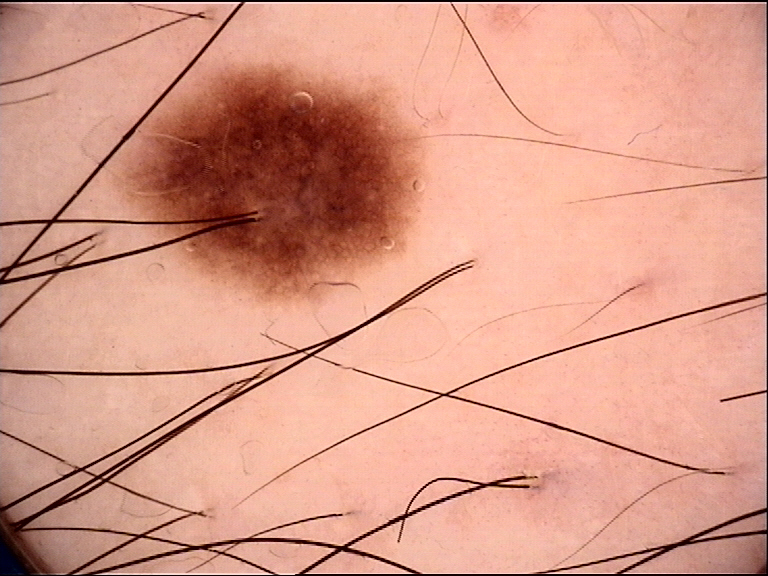The diagnostic label was a junctional nevus.